Close-up view — 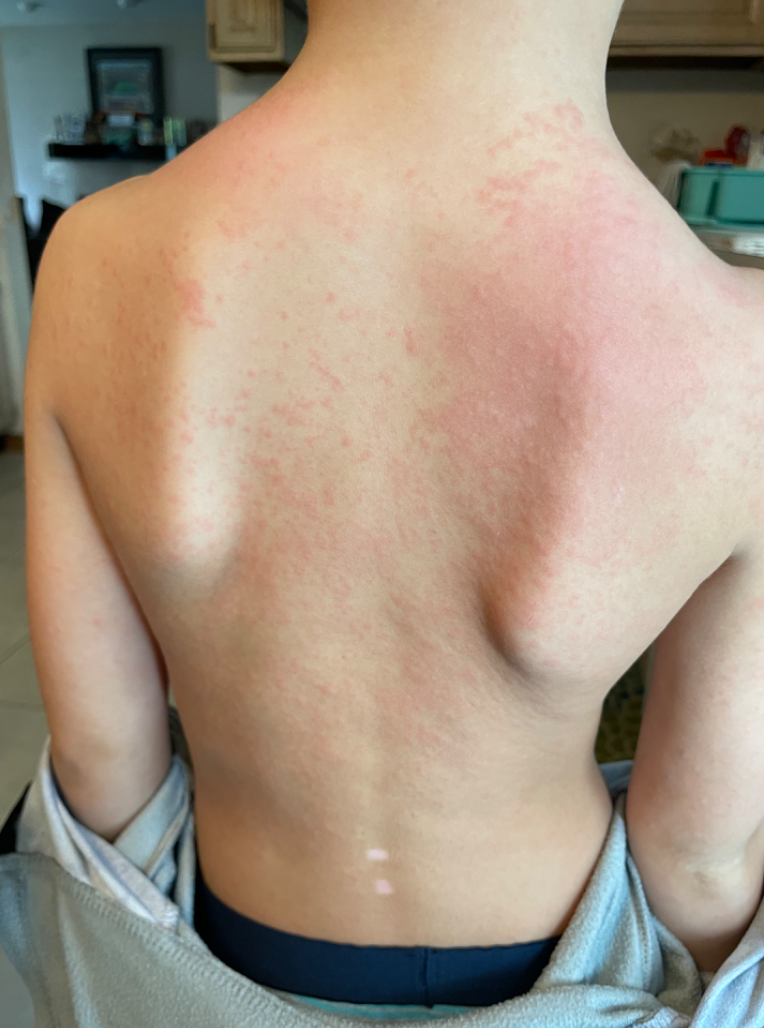Q: What conditions are considered?
A: reviewed remotely by one dermatologist: consistent with Urticaria